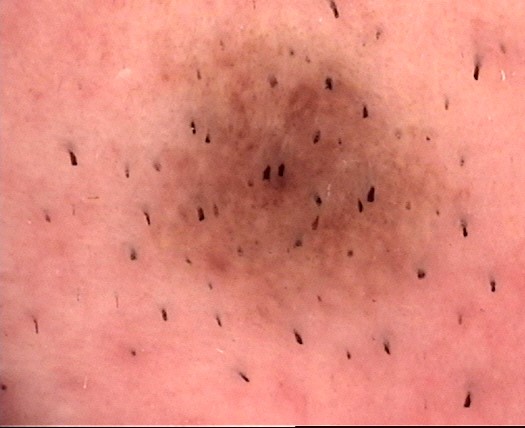Q: What kind of image is this?
A: dermatoscopy
Q: What kind of lesion is this?
A: banal, compound
Q: What is the diagnosis?
A: Miescher nevus (expert consensus)